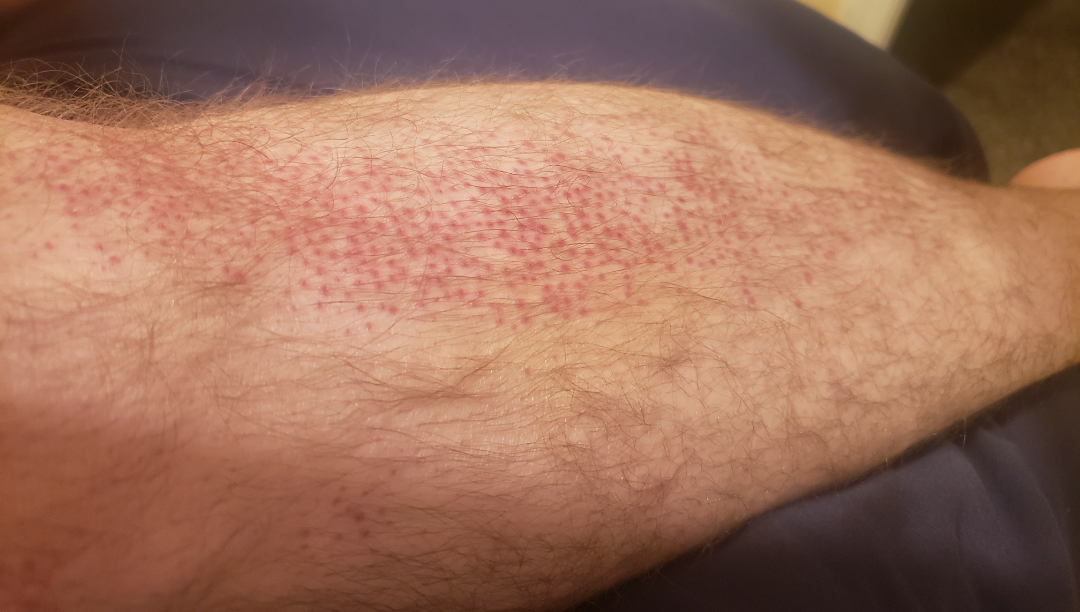<report>
  <patient>male, age 50–59</patient>
  <body_site>leg</body_site>
  <shot_type>at an angle</shot_type>
  <differential>
    <leading>Folliculitis</leading>
    <unlikely>Pigmented purpuric eruption, Amyloidosis of skin, Irritant Contact Dermatitis, Leukocytoclastic Vasculitis, Pityriasis rubra pilaris, Eczema, scurvy</unlikely>
  </differential>
</report>